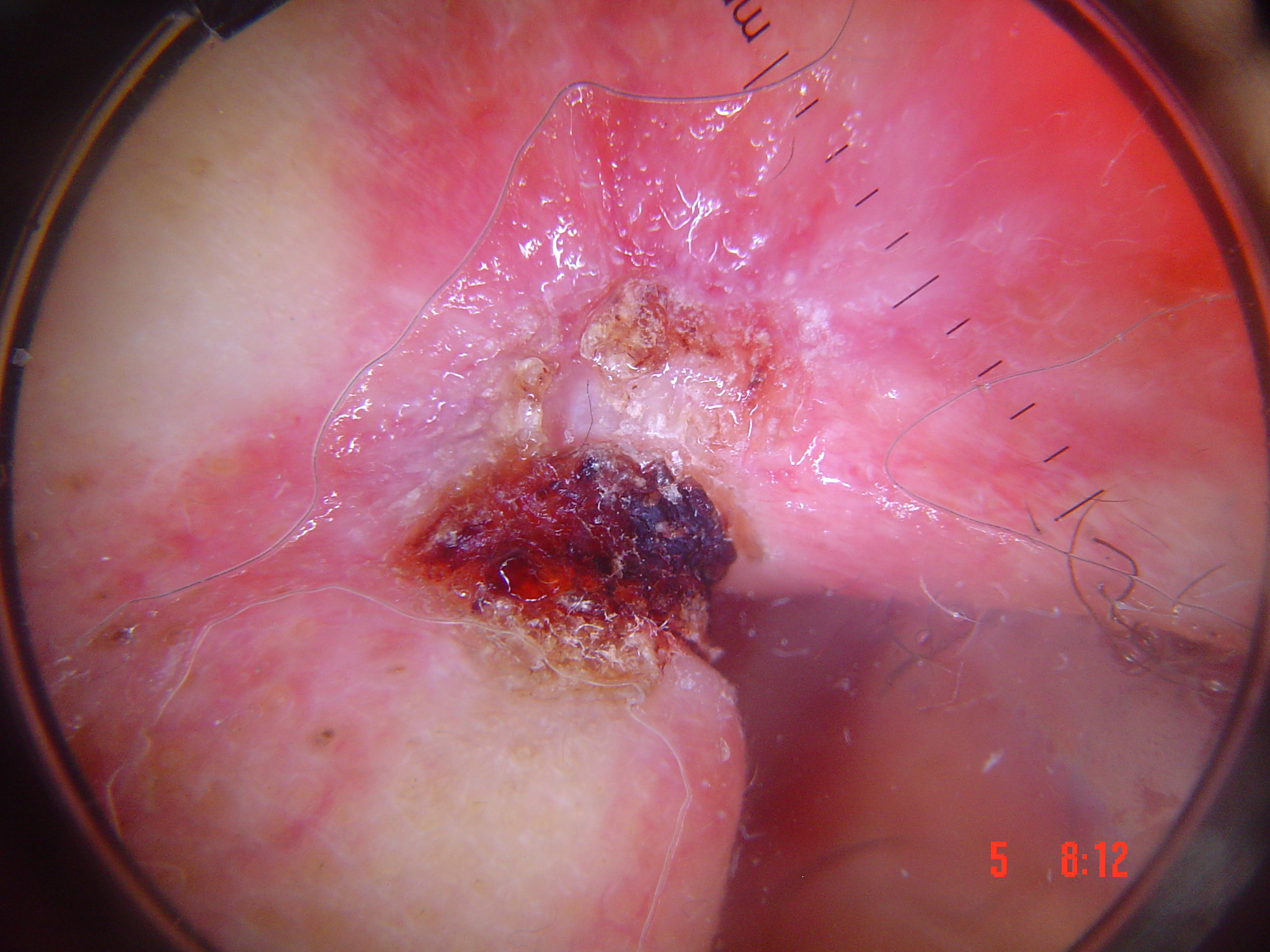image type = dermatoscopy
lesion type = keratinocytic
class = basal cell carcinoma (biopsy-proven)